The patient indicates bleeding, burning, enlargement and itching · the lesion is described as raised or bumpy · the affected area is the back of the hand · the condition has been present for three to twelve months · an image taken at a distance — 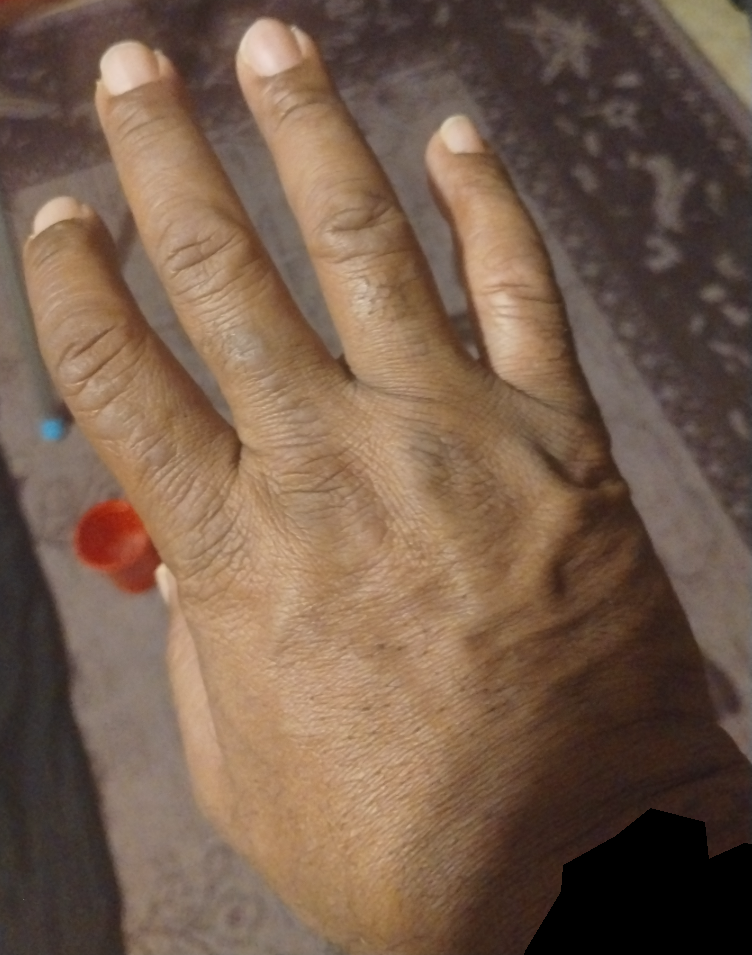assessment: ungradable on photographic review